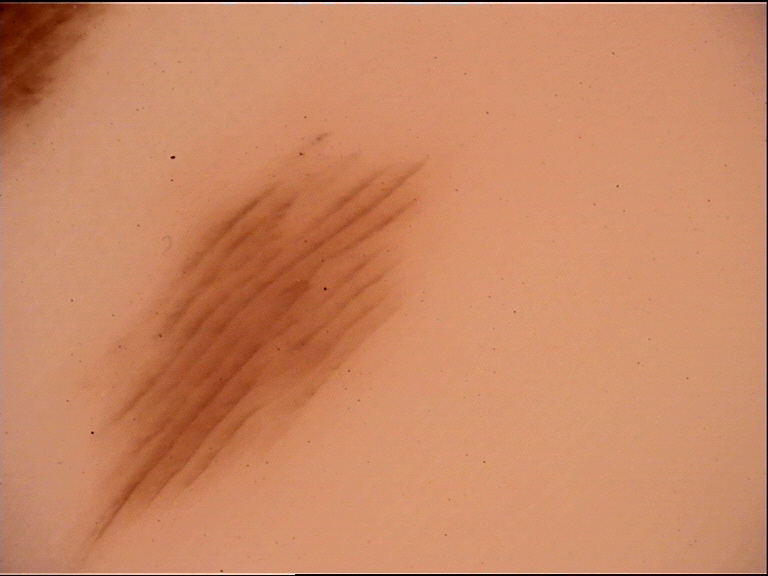Case:
A dermoscopy image of a single skin lesion. This is a banal lesion.
Conclusion:
Diagnosed as an acral junctional nevus.